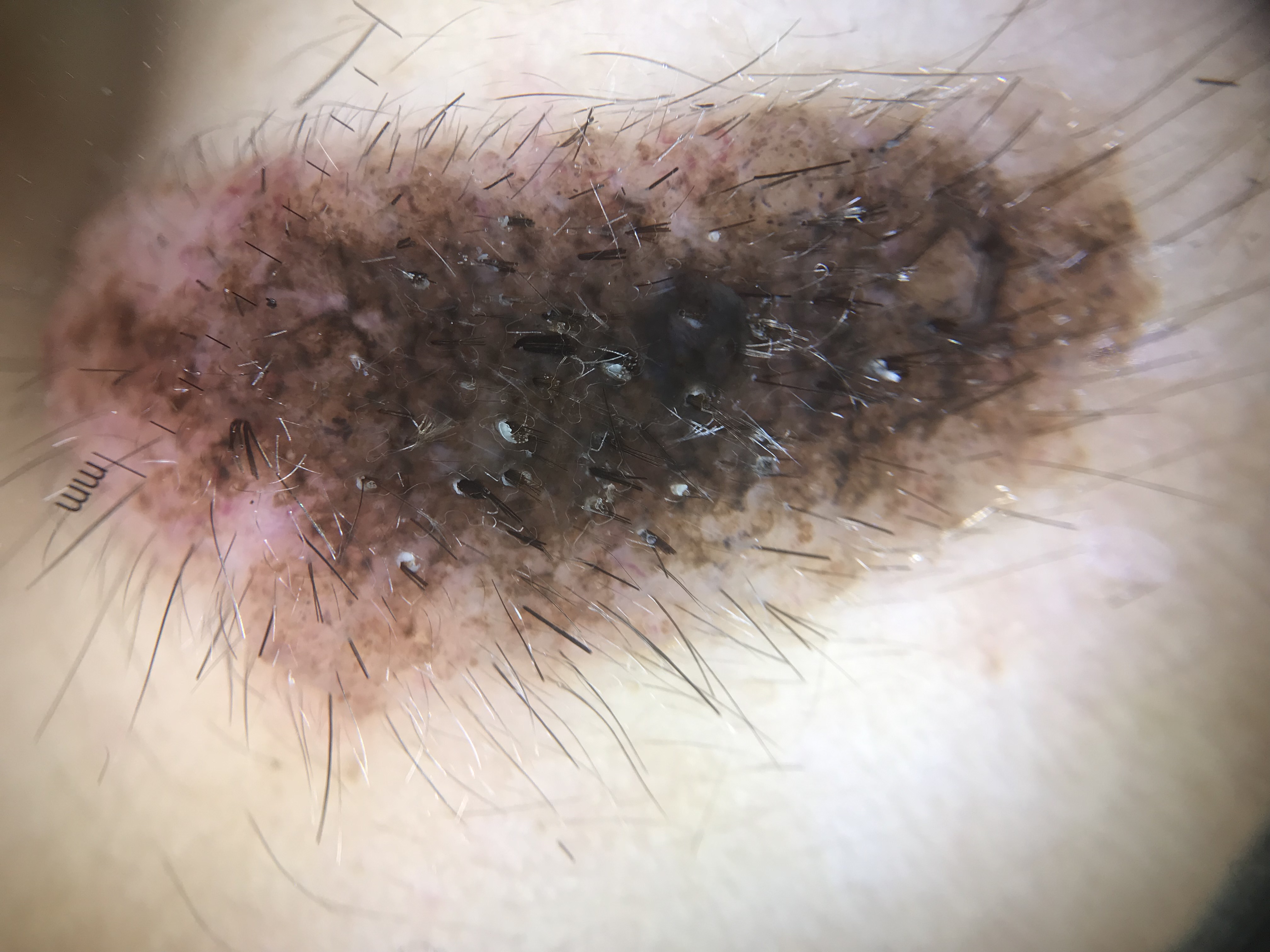assessment = congenital compound nevus (expert consensus).